A female patient 35 years of age · the chart records prior malignancy (patient or family) · a clinical close-up photograph of a skin lesion · recorded as Fitzpatrick skin type II.
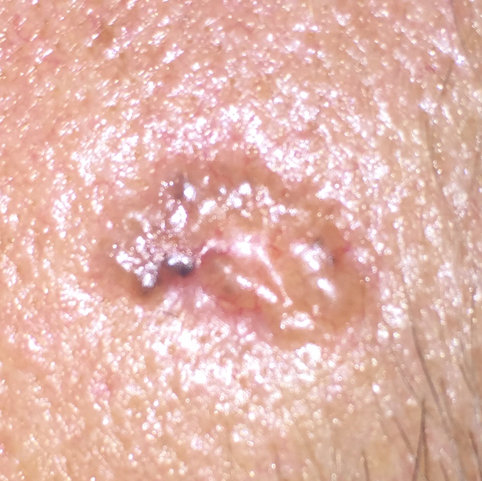Summary:
The lesion measures approximately 11 × 7 mm. By the patient's account, the lesion is elevated.
Pathology:
The biopsy diagnosis was a basal cell carcinoma.